The photograph is a close-up of the affected area:
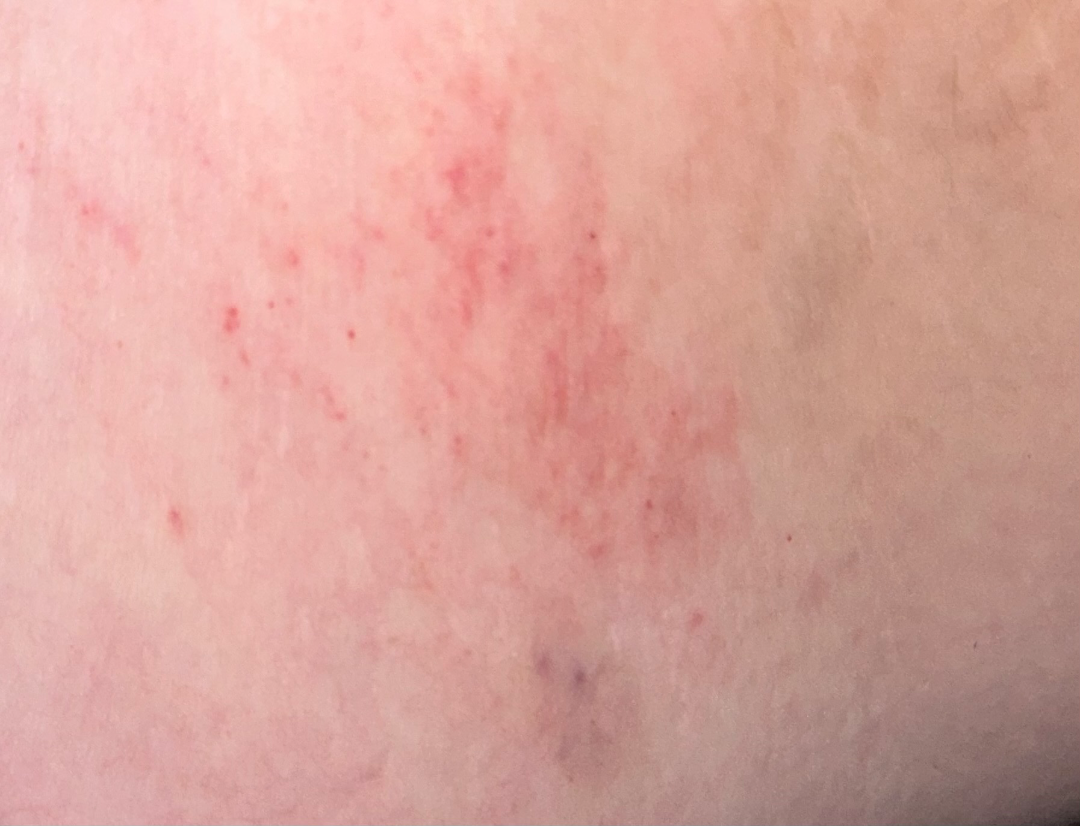{
  "differential": {
    "leading": [
      "Eczema"
    ]
  }
}